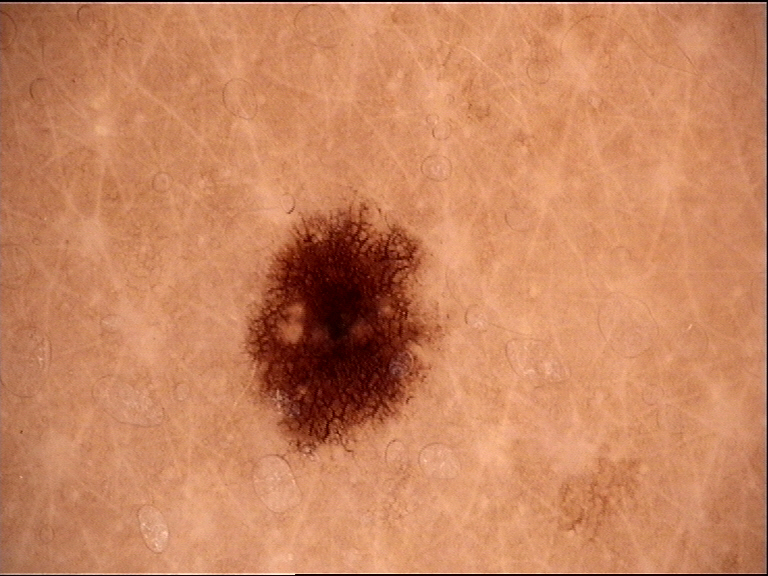Case:
A dermoscopic close-up of a skin lesion. The morphology is that of a banal lesion.
Conclusion:
The diagnosis was a junctional nevus.